A skin lesion imaged with a dermatoscope.
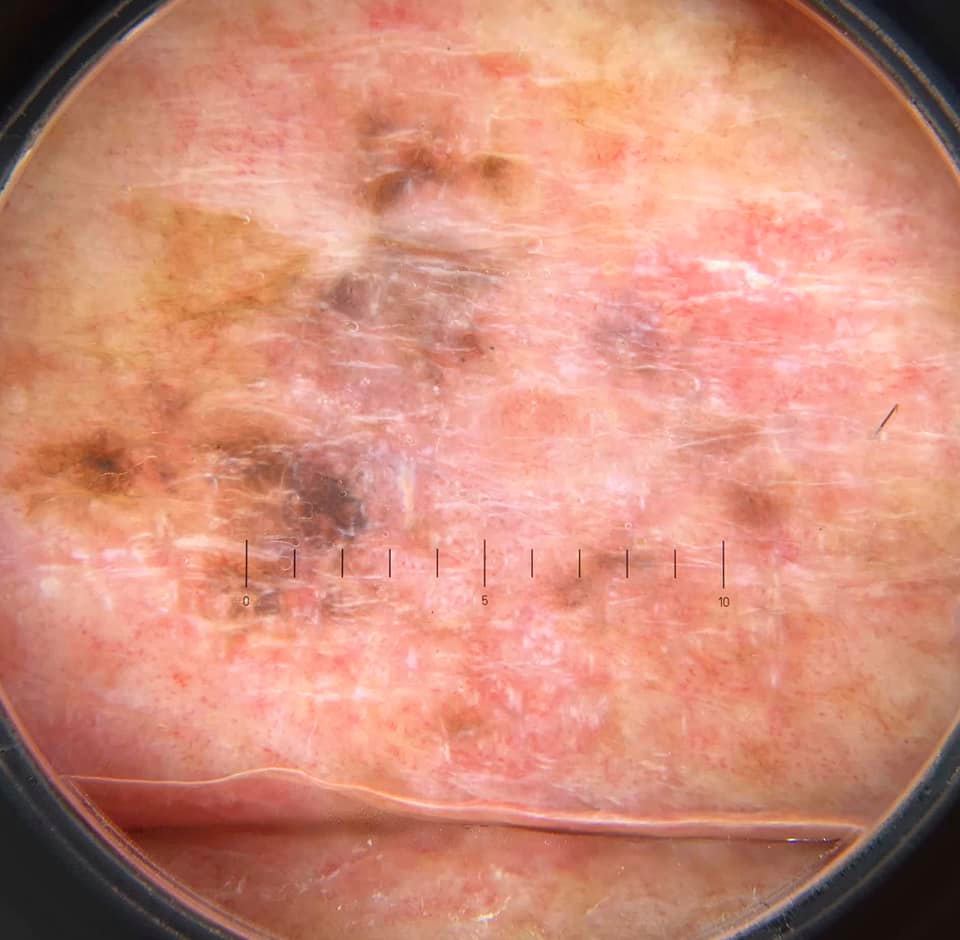Histopathology confirmed a lentigo maligna.